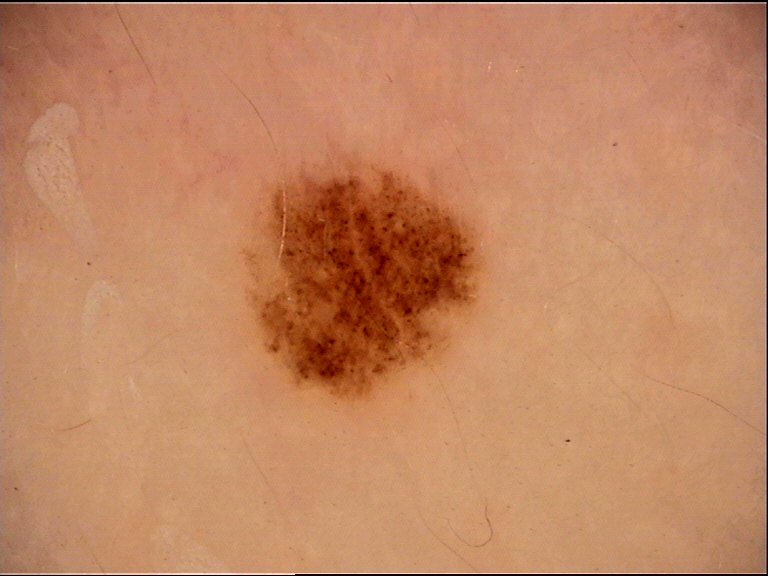Case:
A dermoscopic photograph of a skin lesion.
Impression:
Labeled as a dysplastic junctional nevus.